The leg and arm are involved, symptoms reported: enlargement and itching, an image taken at an angle, the patient considered this a rash.
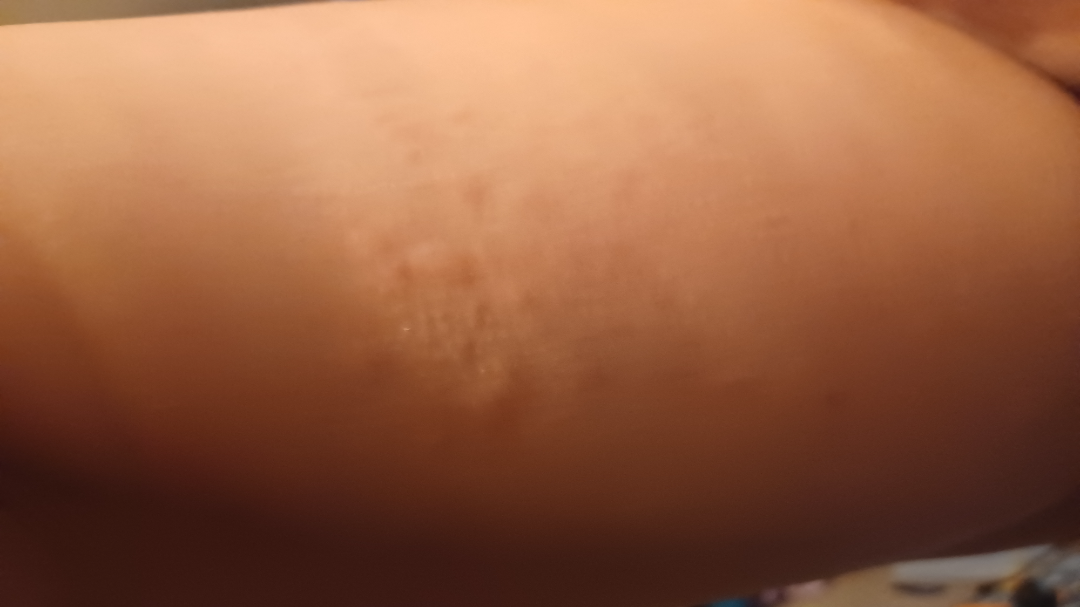Impression:
The condition could not be reliably identified from the image.